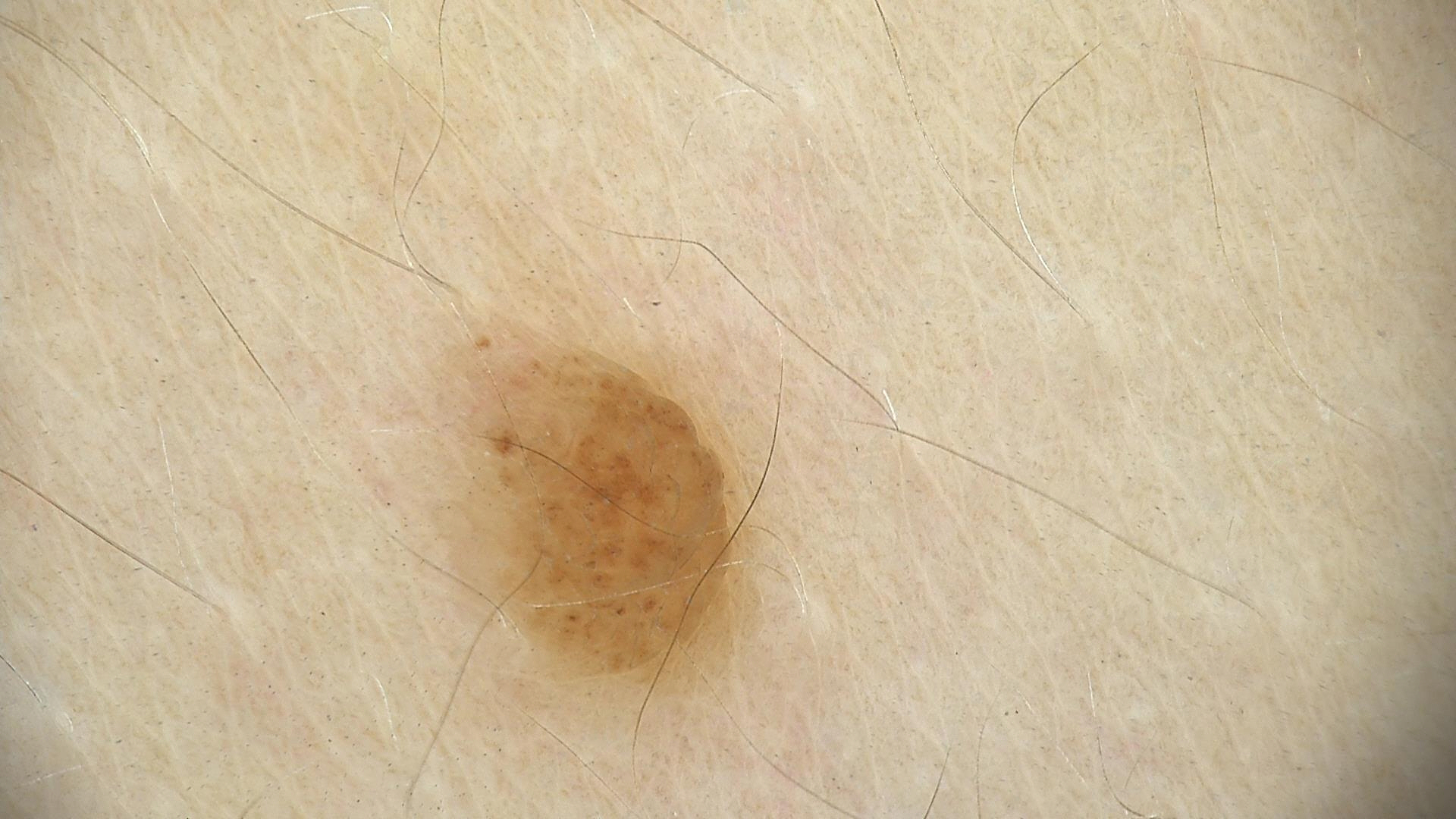image = dermatoscopy, assessment = dermal nevus (expert consensus).